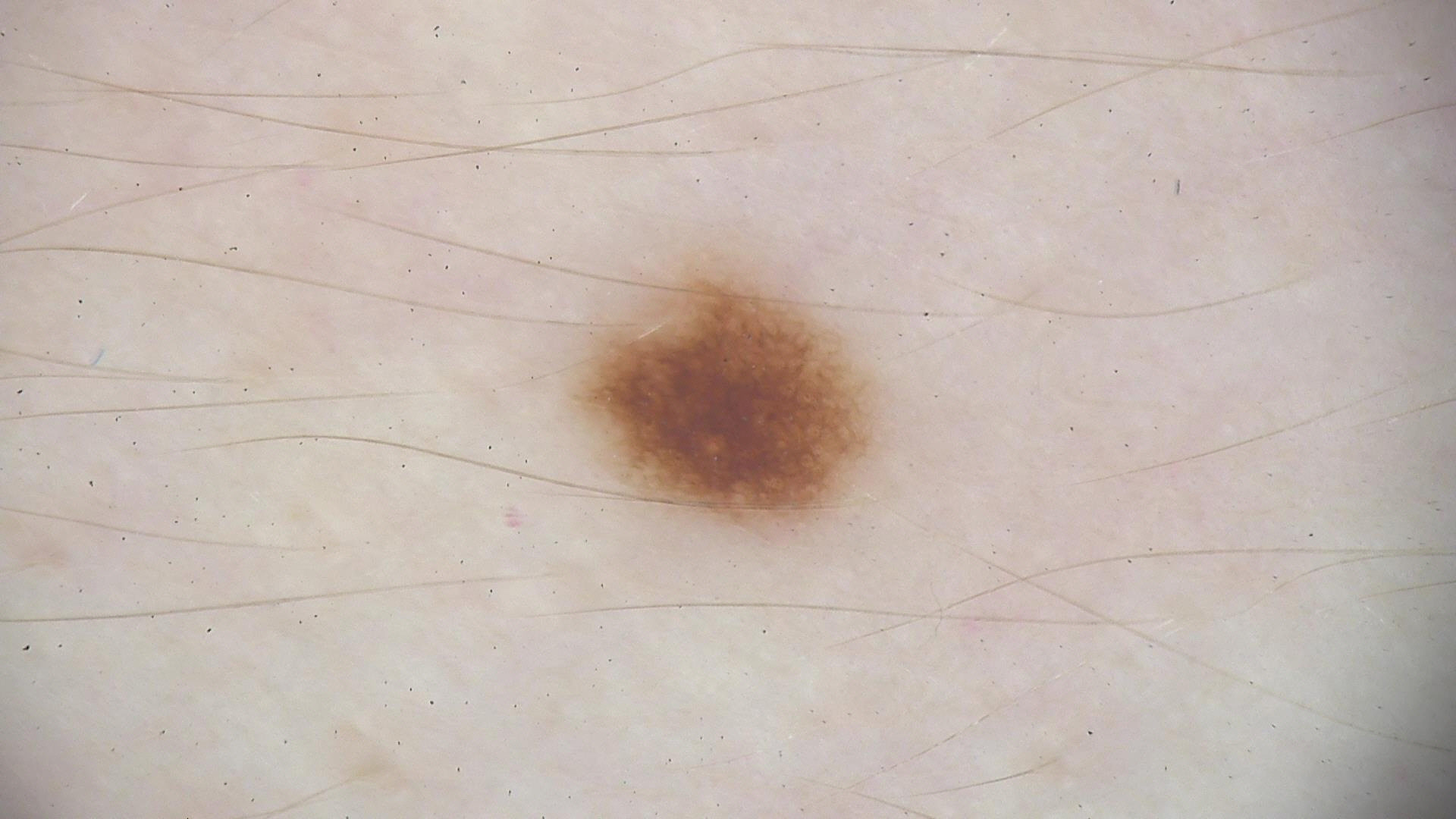image type = dermoscopy
label = dysplastic junctional nevus (expert consensus)